A dermoscopic image of a skin lesion.
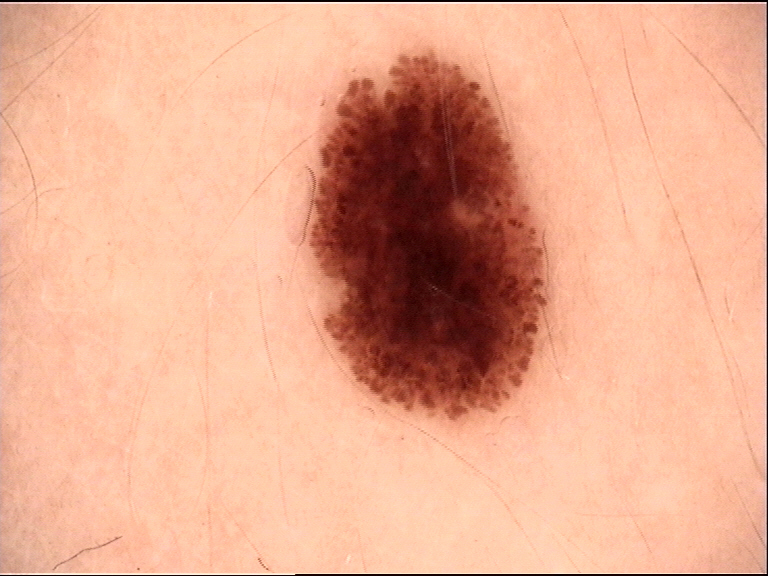Q: What was the diagnostic impression?
A: dysplastic junctional nevus (expert consensus)